A dermoscopic image of a skin lesion:
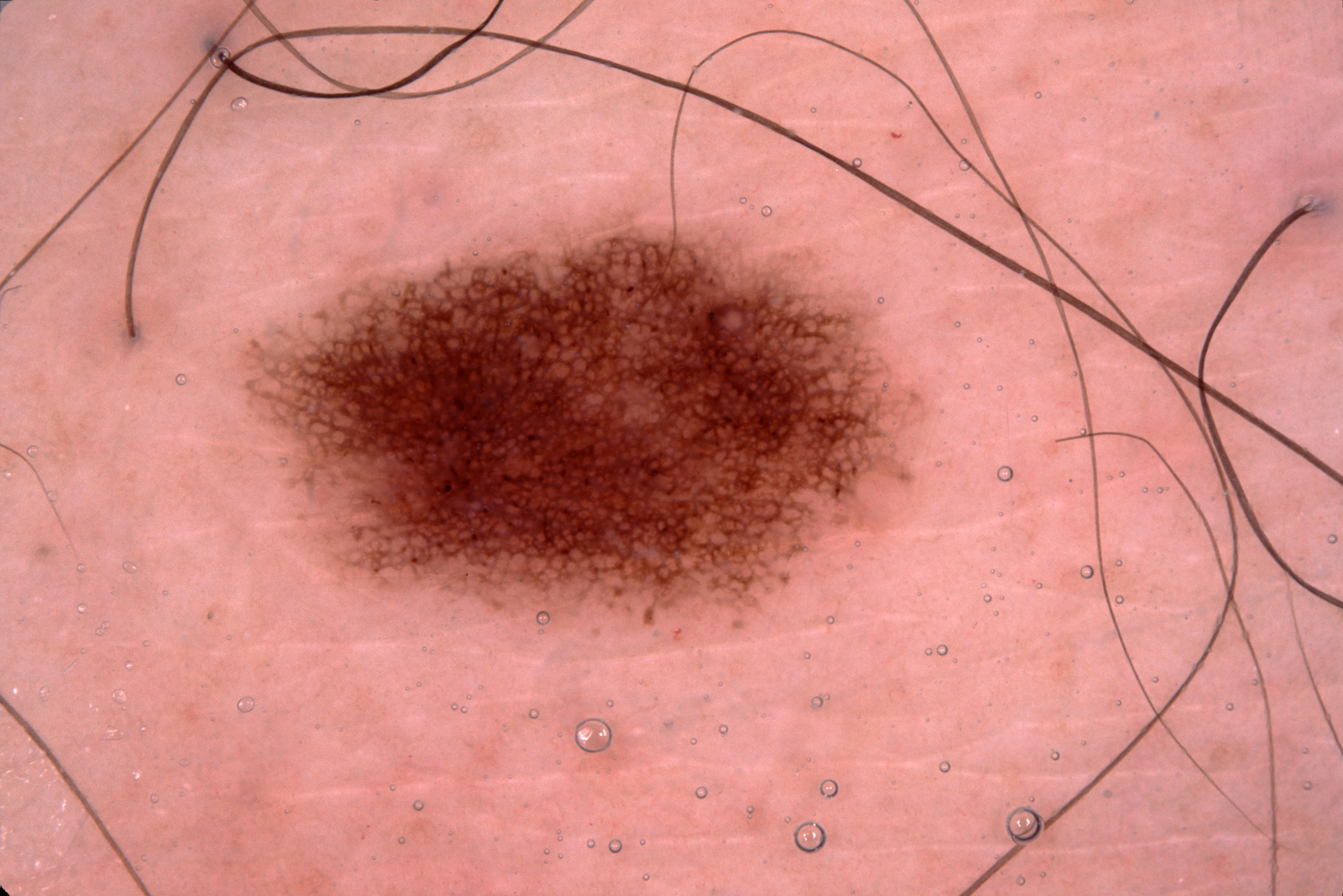Q: What dermoscopic features are present?
A: pigment network; absent: milia-like cysts, negative network, and streaks
Q: Where is the lesion in the image?
A: [243,177,911,626]
Q: How large is the lesion within the image?
A: ~15% of the field
Q: What is this lesion?
A: a melanocytic nevus, a benign skin lesion